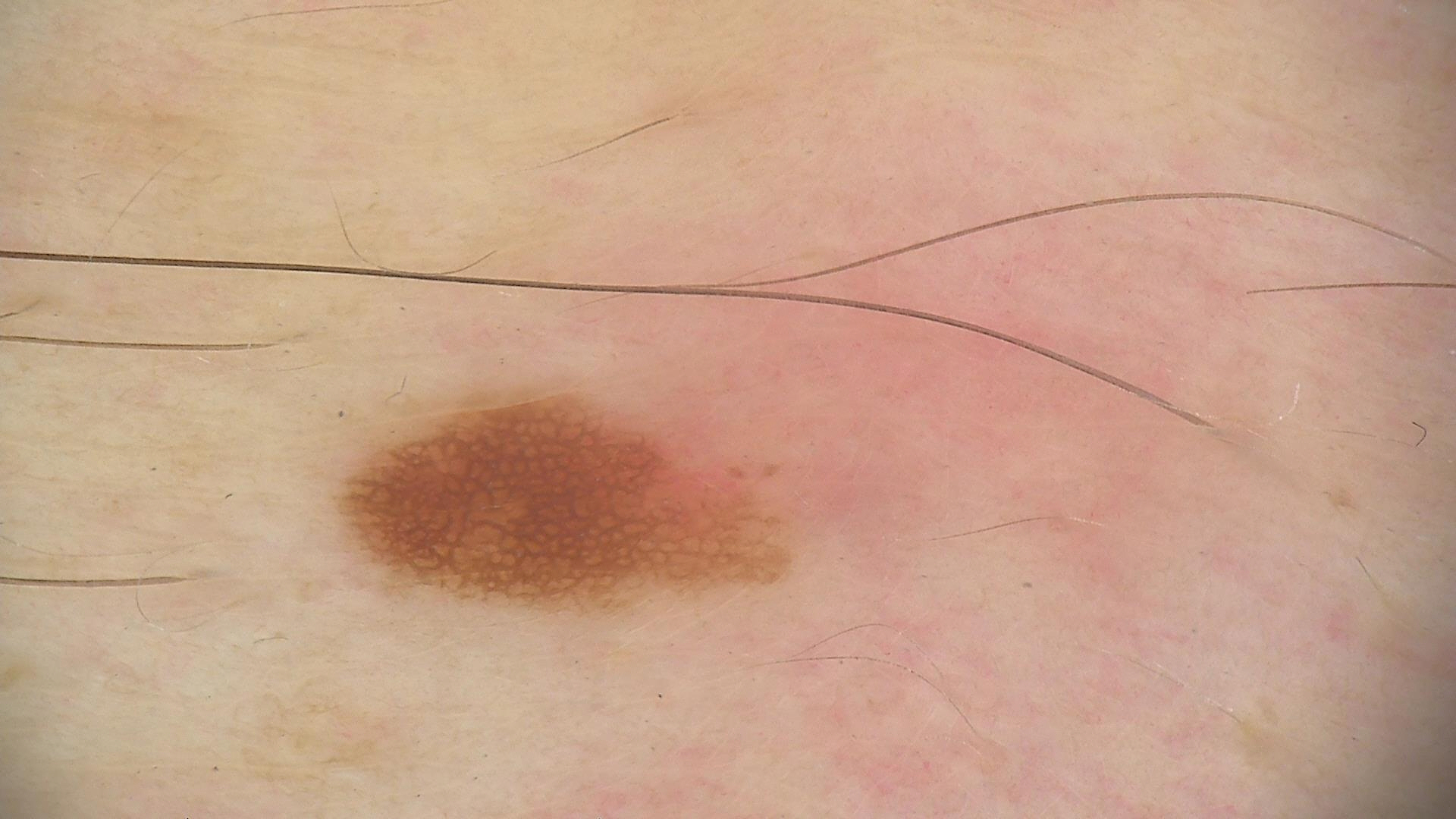{
  "image": "dermoscopy",
  "diagnosis": {
    "name": "dysplastic junctional nevus",
    "code": "jd",
    "malignancy": "benign",
    "super_class": "melanocytic",
    "confirmation": "expert consensus"
  }
}